A smartphone photograph of a skin lesion; a subject 67 years of age: 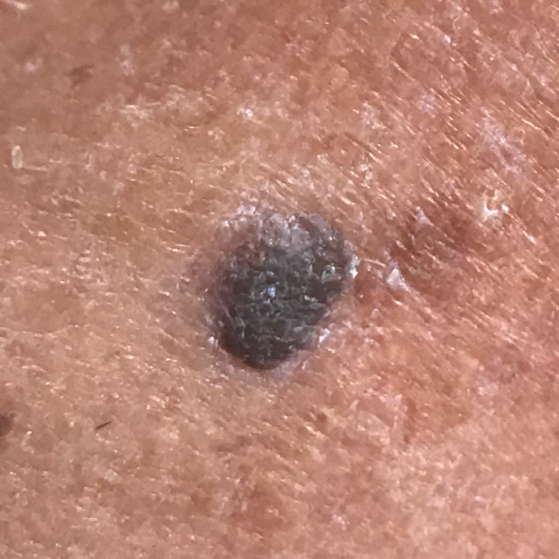{
  "lesion_location": "the face",
  "diagnosis": {
    "name": "seborrheic keratosis",
    "code": "SEK",
    "malignancy": "benign",
    "confirmation": "clinical consensus"
  }
}